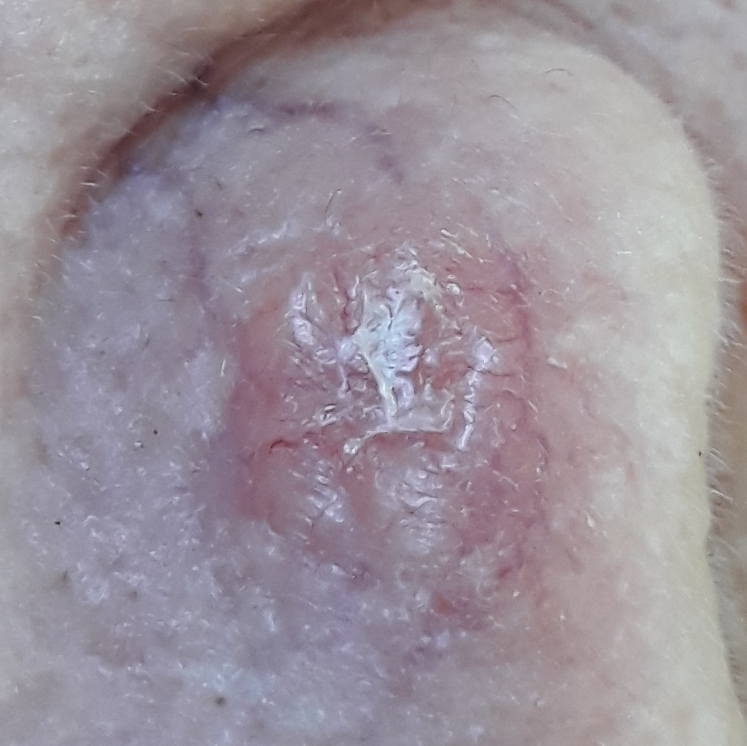  skin_type: II
  patient:
    age: 79
    gender: female
  lesion_location: the nose
  lesion_size:
    diameter_1_mm: 9.0
    diameter_2_mm: 6.0
  symptoms:
    present:
      - elevation
      - itching
  diagnosis:
    name: basal cell carcinoma
    code: BCC
    malignancy: malignant
    confirmation: histopathology